Dermoscopy of a skin lesion.
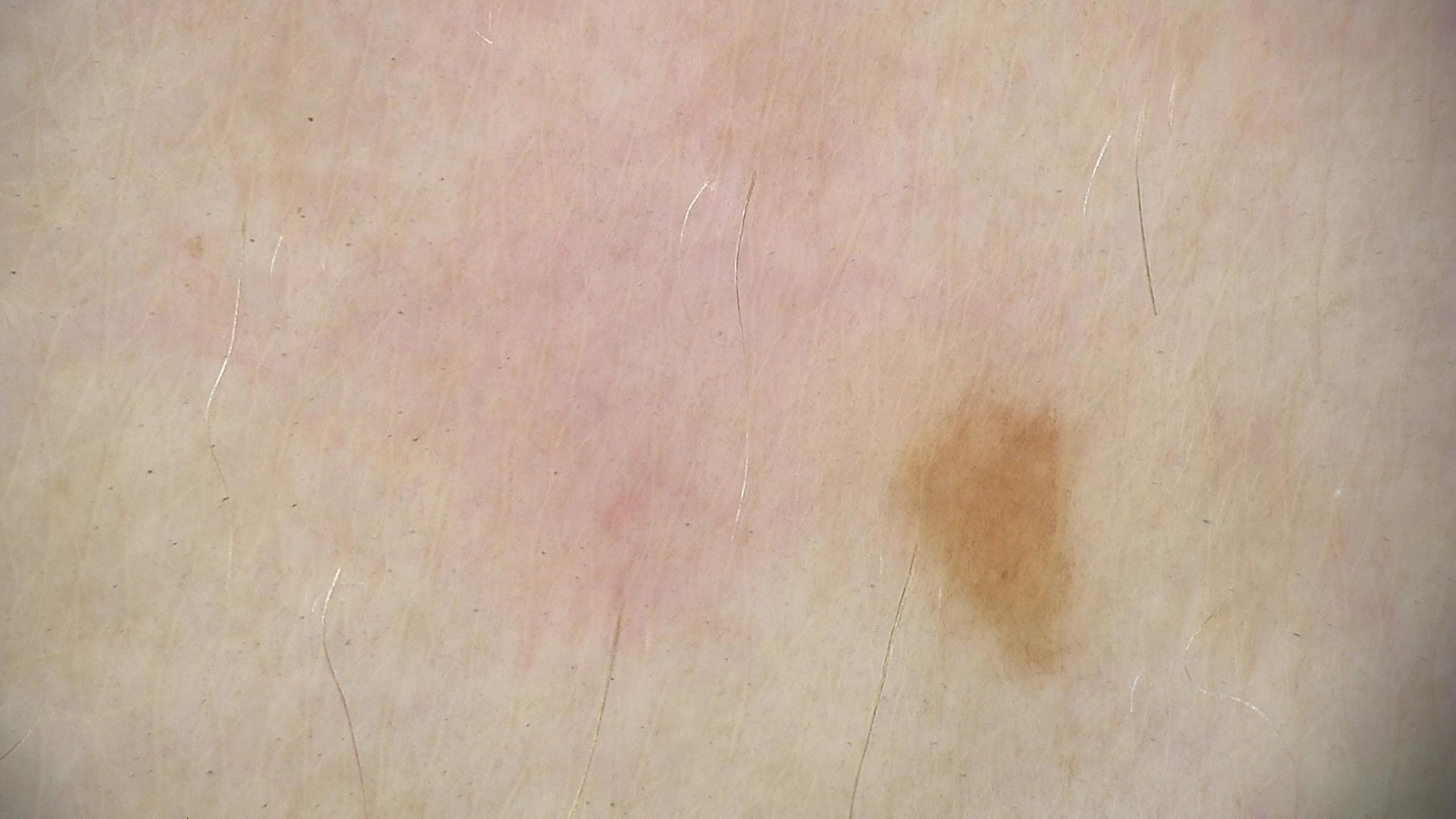| field | value |
|---|---|
| diagnosis | junctional nevus (expert consensus) |